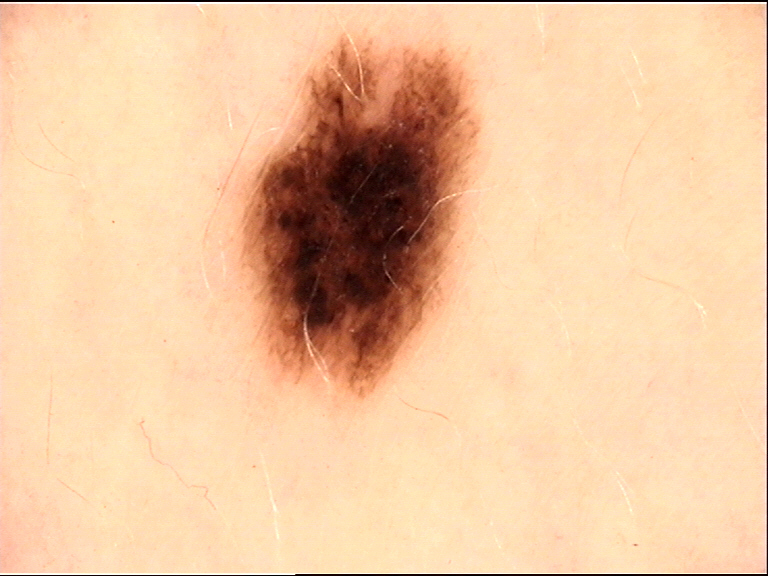* image type: dermatoscopy
* diagnostic label: dysplastic junctional nevus (expert consensus)